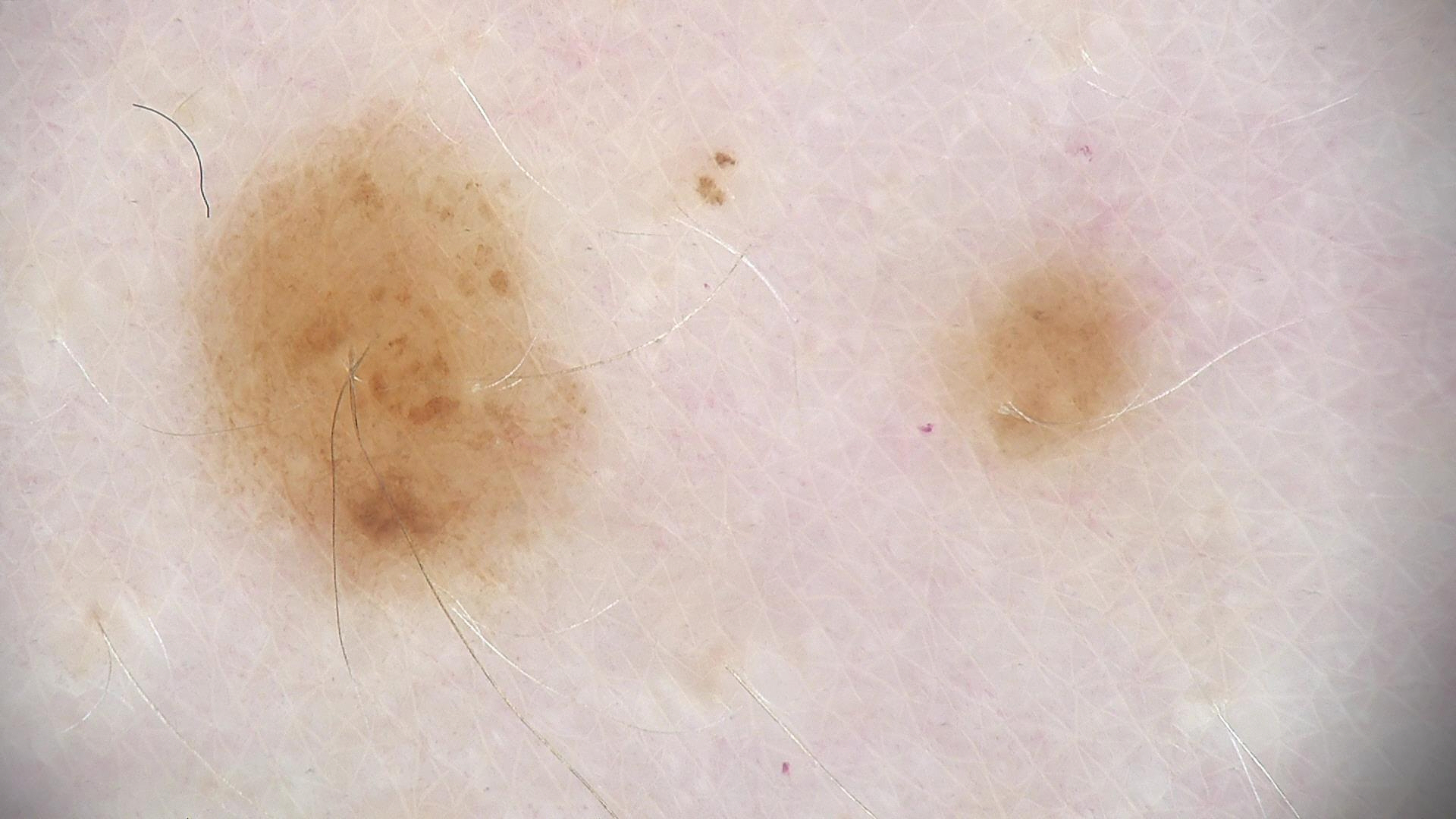  diagnosis:
    name: dysplastic junctional nevus
    code: jd
    malignancy: benign
    super_class: melanocytic
    confirmation: expert consensus